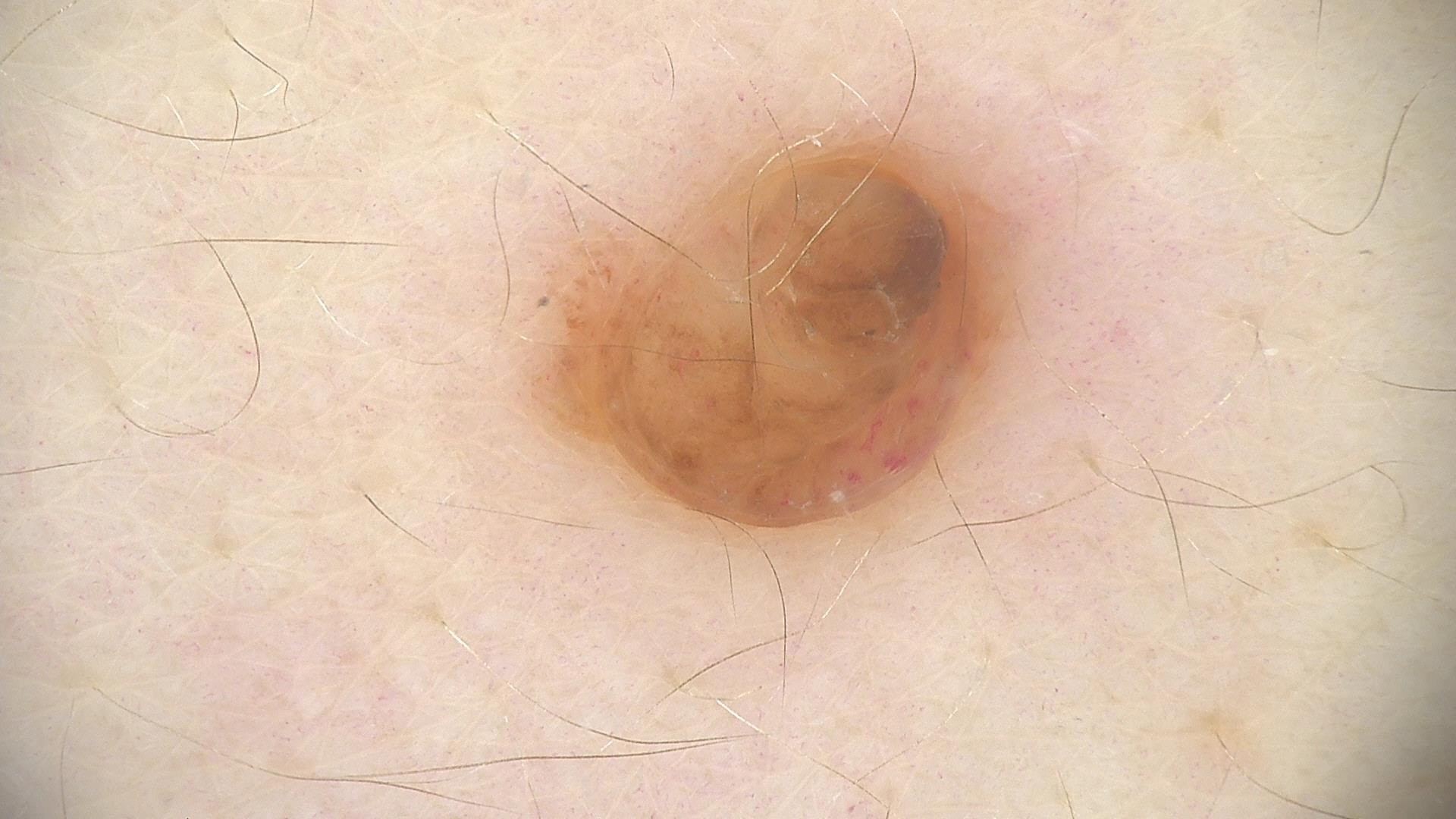image type = dermatoscopy; diagnosis = dermal nevus (expert consensus).